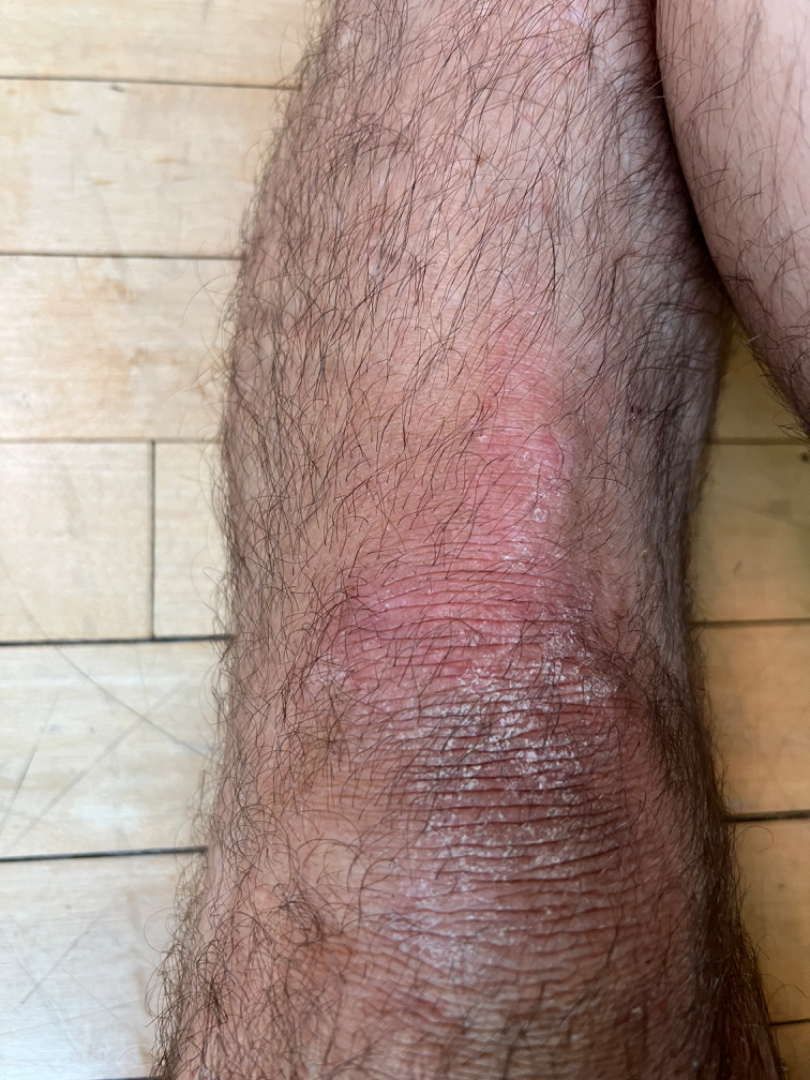| key | value |
|---|---|
| framing | close-up |
| lesion texture | raised or bumpy and rough or flaky |
| self-categorized as | a rash |
| constitutional symptoms | none reported |
| location | leg |
| reported symptoms | itching |
| assessment | the impression on review was Psoriasis |